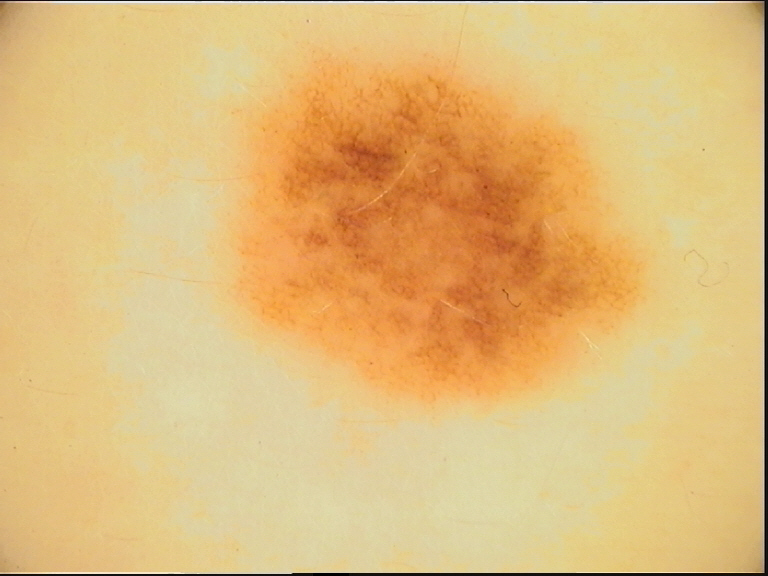- assessment — dysplastic junctional nevus (expert consensus)